Skin tone: FST II; the lesion involves the top or side of the foot; female contributor, age 60–69; the lesion is described as raised or bumpy; the photograph was taken at an angle; the condition has been present for one to four weeks: 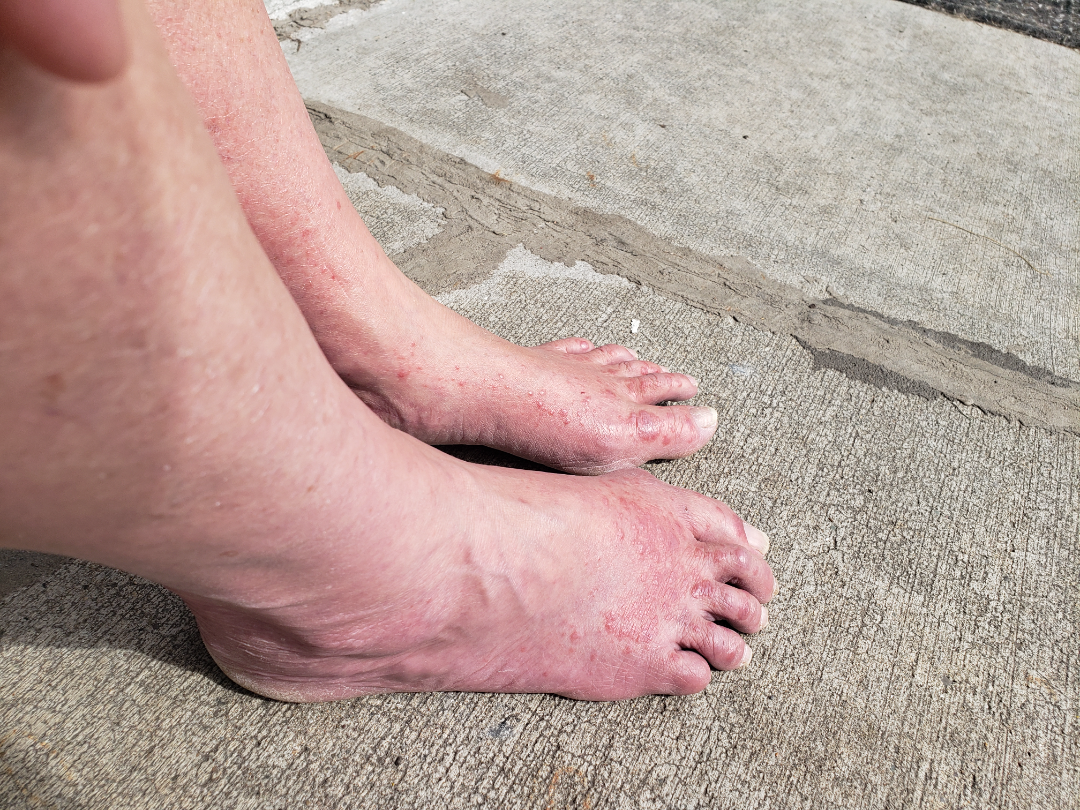impression = the leading consideration is Lichen planus/lichenoid eruption; lower on the differential is Granuloma annulare; less probable is Eczema; less likely is Allergic Contact Dermatitis